A dermoscopic close-up of a skin lesion.
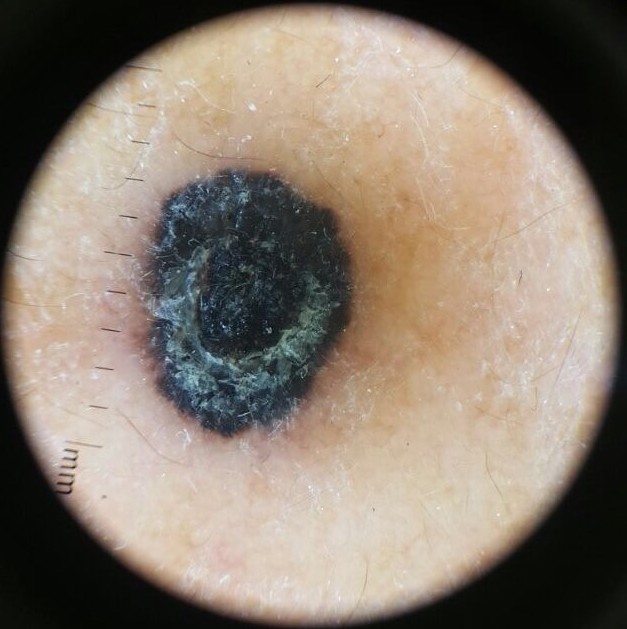{
  "diagnosis": {
    "name": "melanoma",
    "code": "mel",
    "malignancy": "malignant",
    "super_class": "melanocytic",
    "confirmation": "histopathology"
  }
}